A dermoscopic view of a skin lesion.
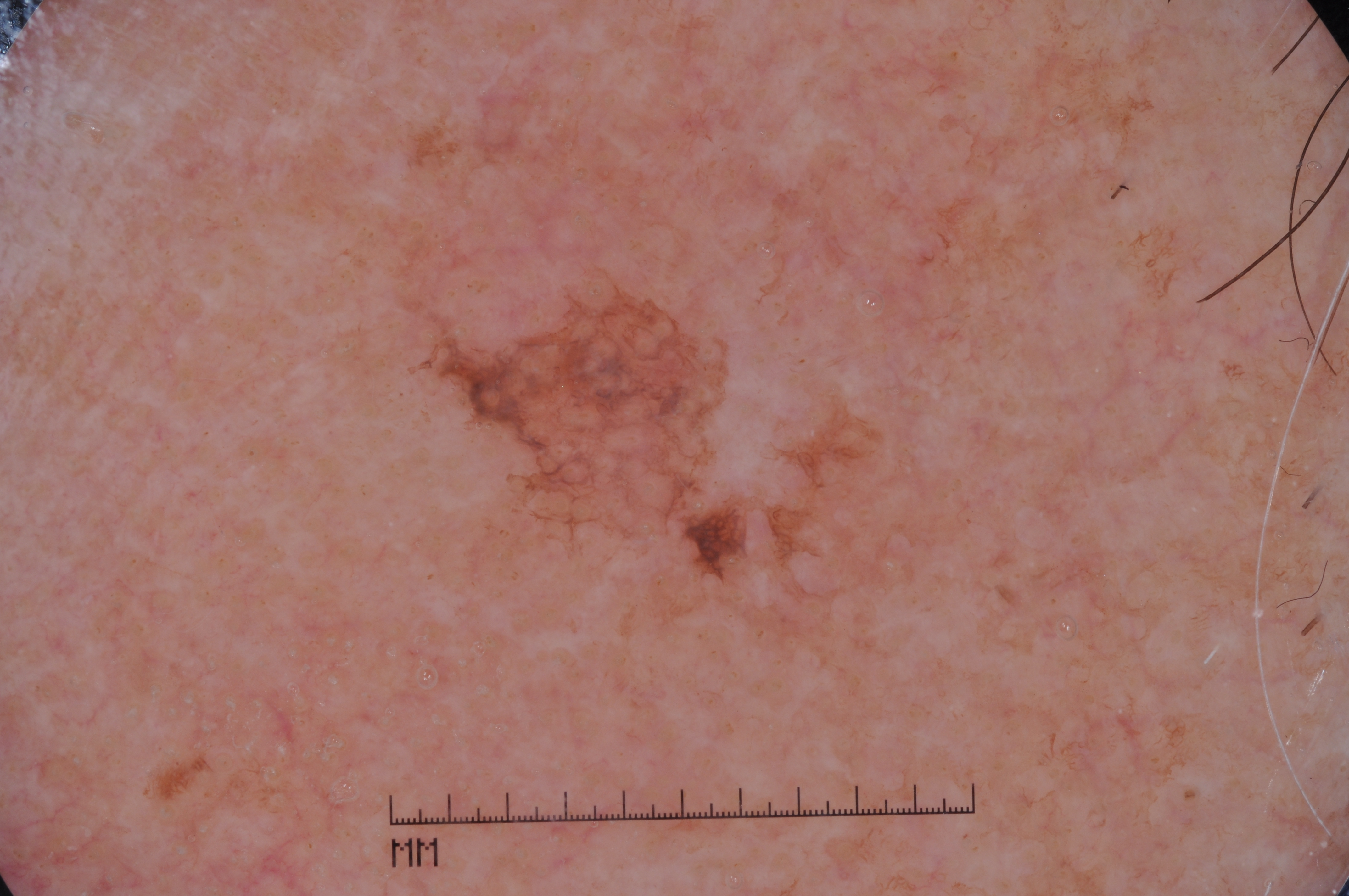Image and clinical context:
The dermoscopic pattern shows pigment network; no milia-like cysts, streaks, or negative network. As (left, top, right, bottom), the lesion is located at 406 271 906 589.
Assessment:
Consistent with a seborrheic keratosis.